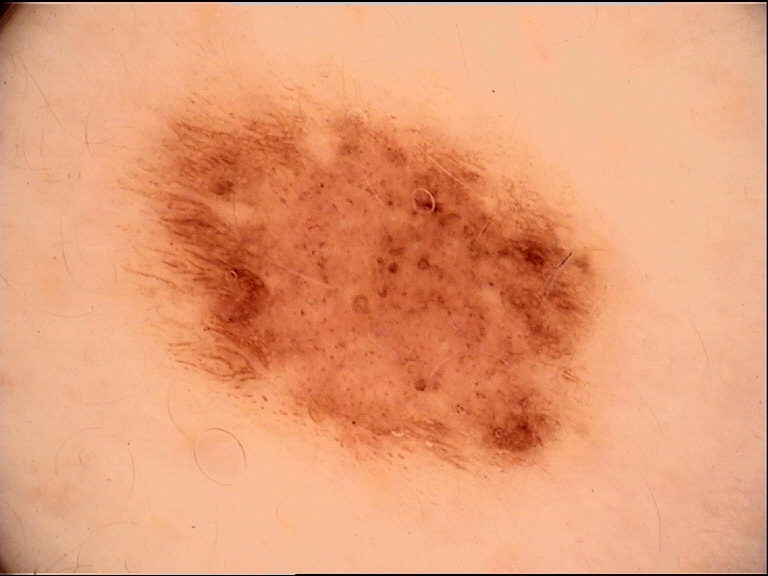Labeled as a dysplastic junctional nevus.